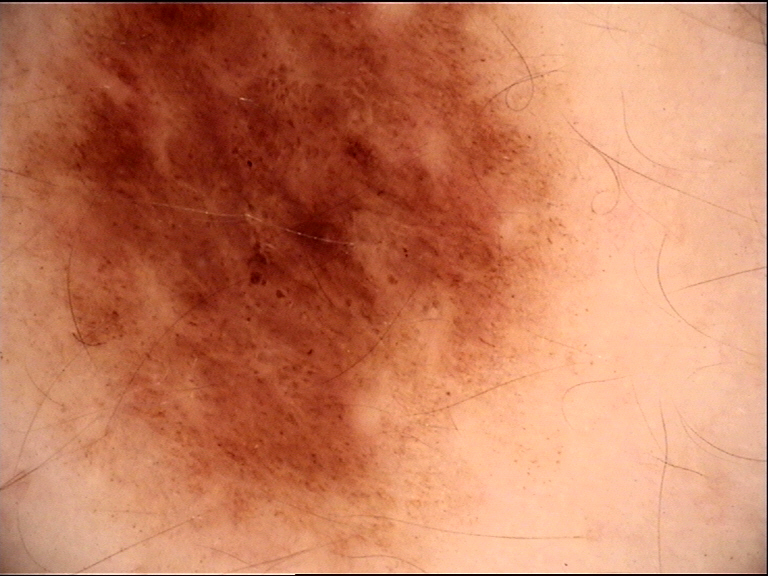{
  "image": "dermoscopy",
  "diagnosis": {
    "name": "dysplastic compound nevus",
    "code": "cd",
    "malignancy": "benign",
    "super_class": "melanocytic",
    "confirmation": "expert consensus"
  }
}